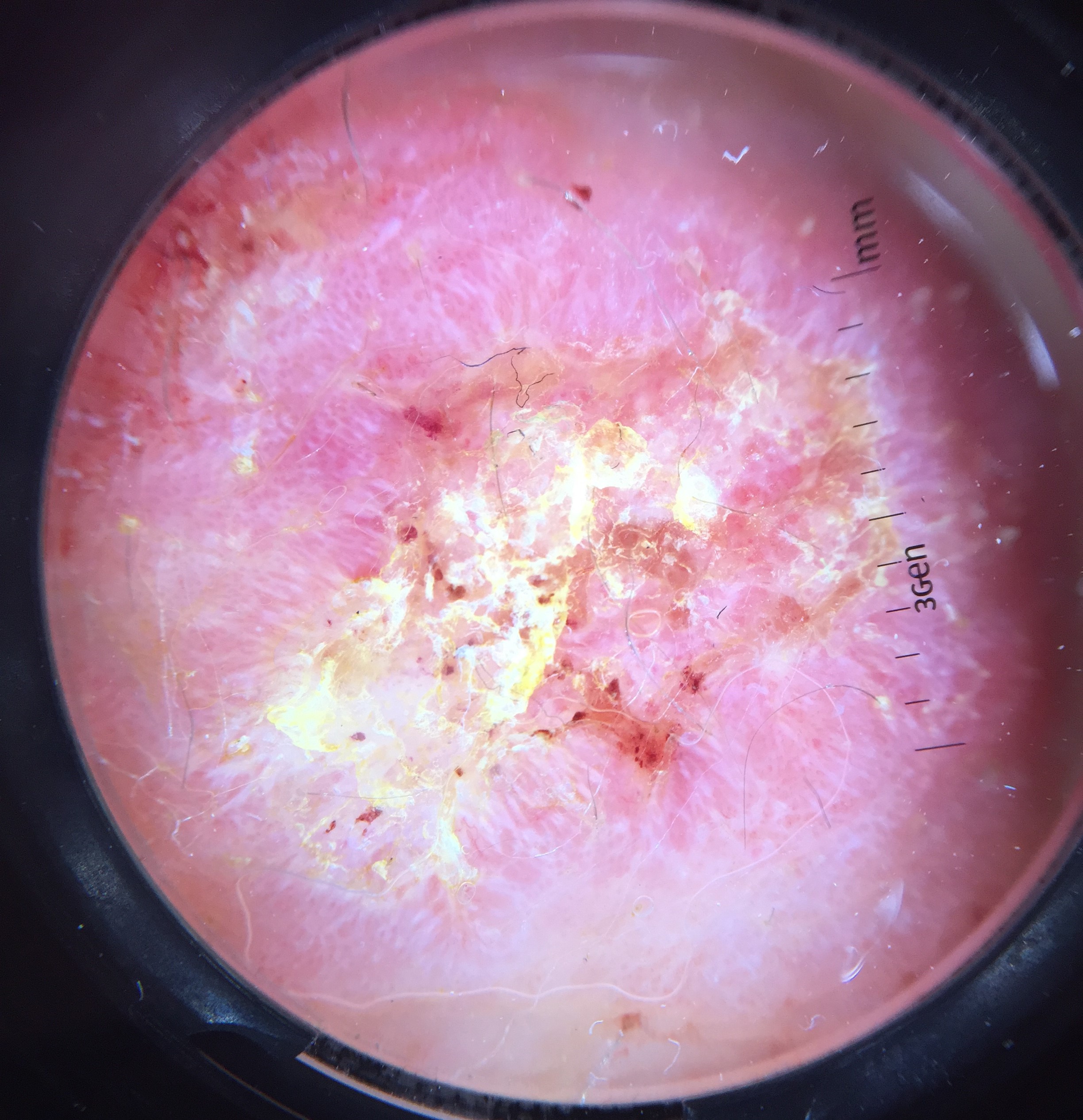A dermatoscopic image of a skin lesion. The morphology is that of a keratinocytic lesion. Biopsy-confirmed as a skin cancer — a squamous cell carcinoma.